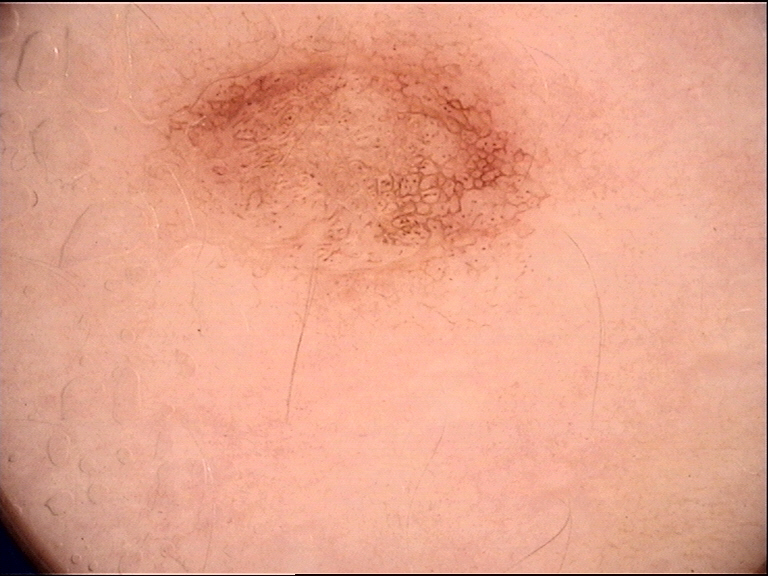Q: What was the diagnostic impression?
A: dysplastic junctional nevus (expert consensus)